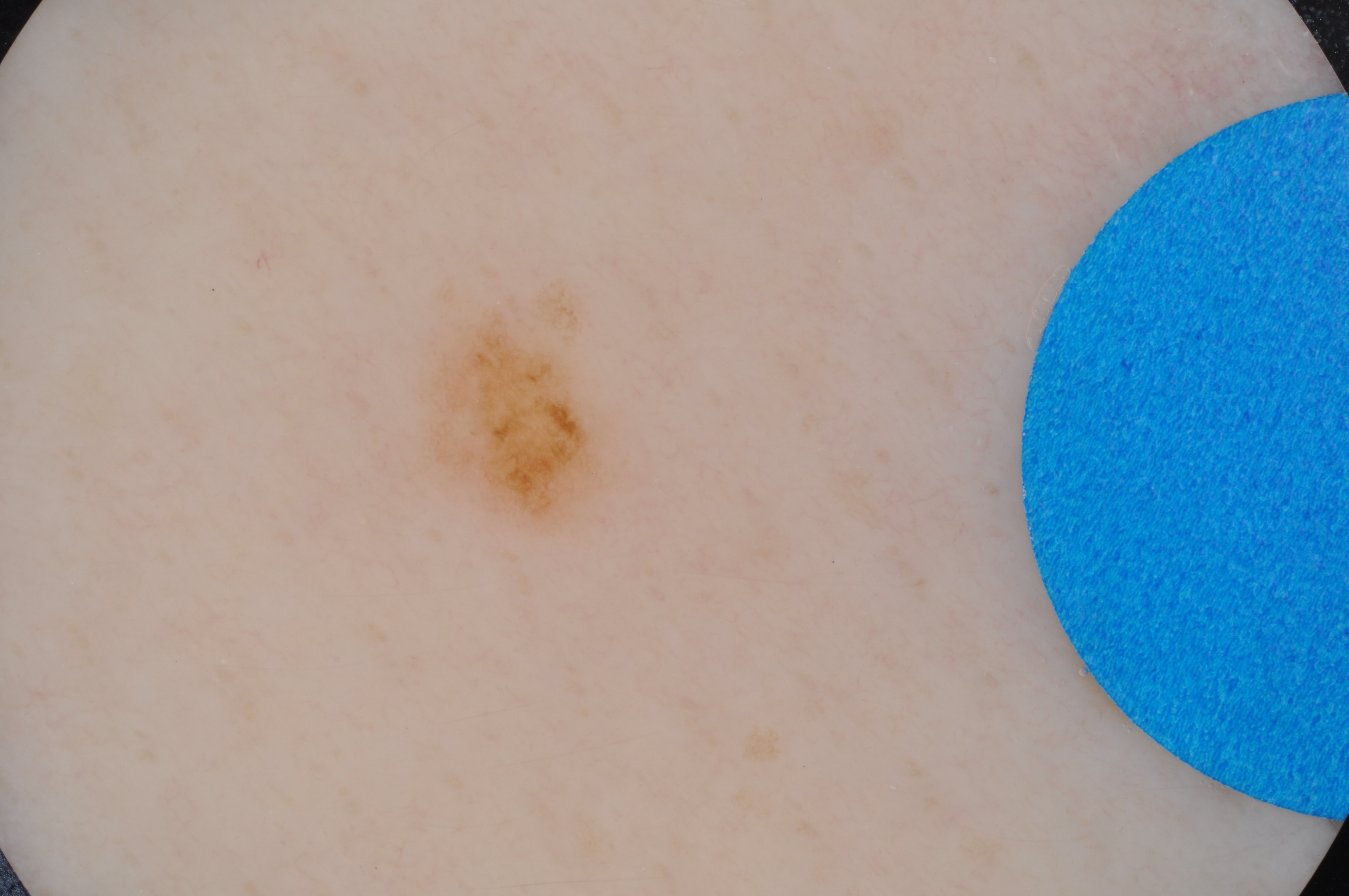Q: What kind of image is this?
A: dermatoscopic image of a skin lesion
Q: Where is the lesion located?
A: [408,257,642,538]
Q: What is the diagnosis?
A: a benign lesion